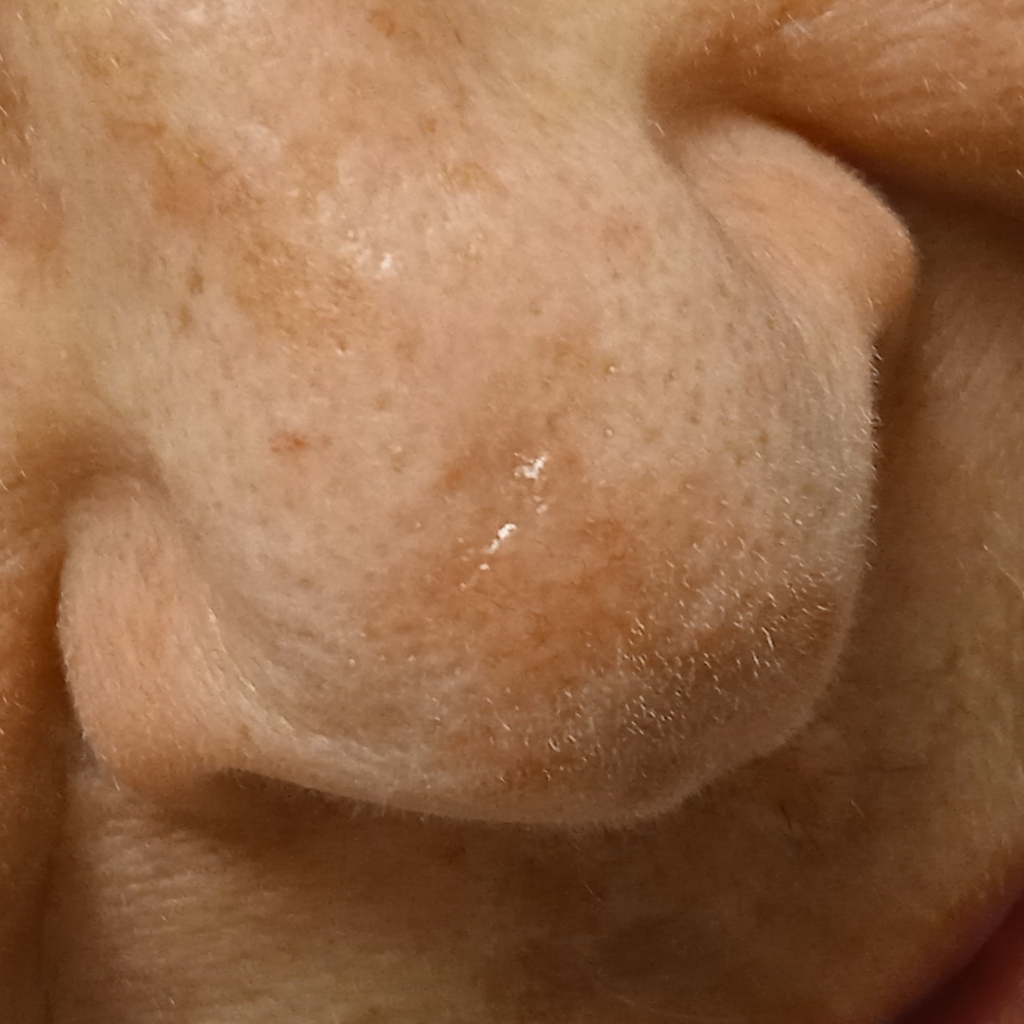pathology=basal cell carcinoma (biopsy-proven).